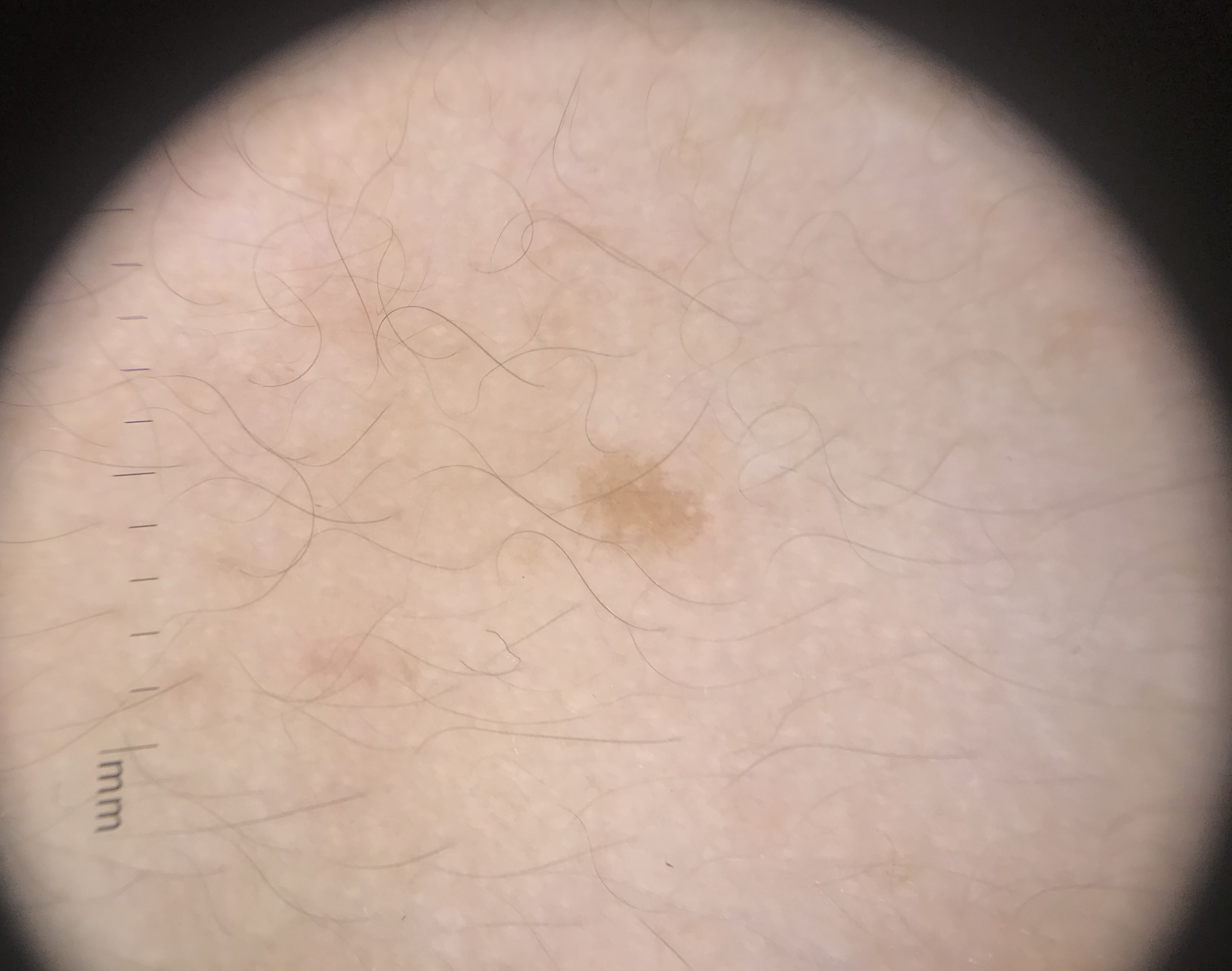{
  "diagnosis": {
    "name": "solar lentigo",
    "code": "sl",
    "malignancy": "benign",
    "super_class": "melanocytic",
    "confirmation": "expert consensus"
  }
}